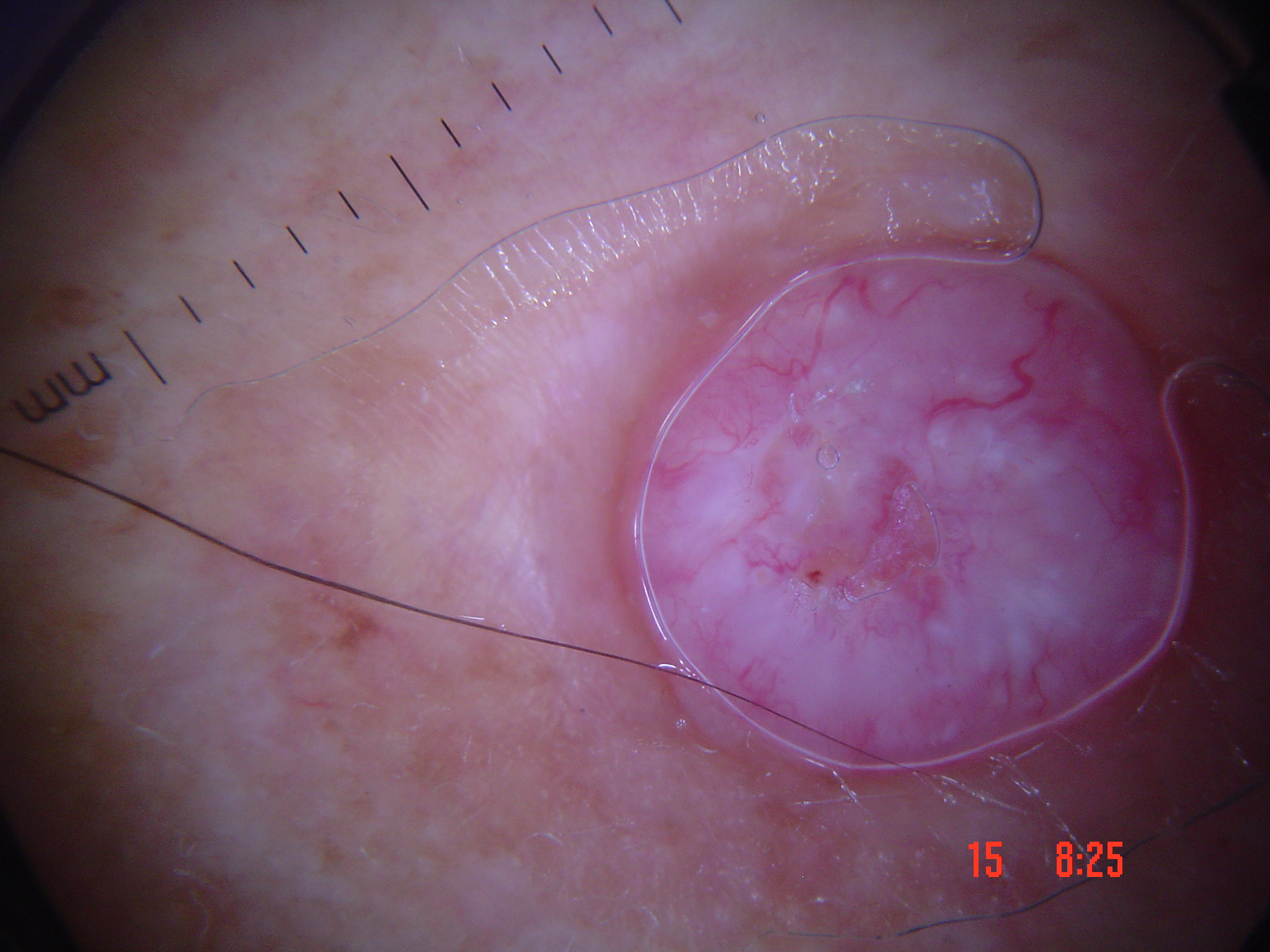Dermoscopy of a skin lesion.
This is a keratinocytic lesion.
The biopsy diagnosis was a malignancy — a squamous cell carcinoma.